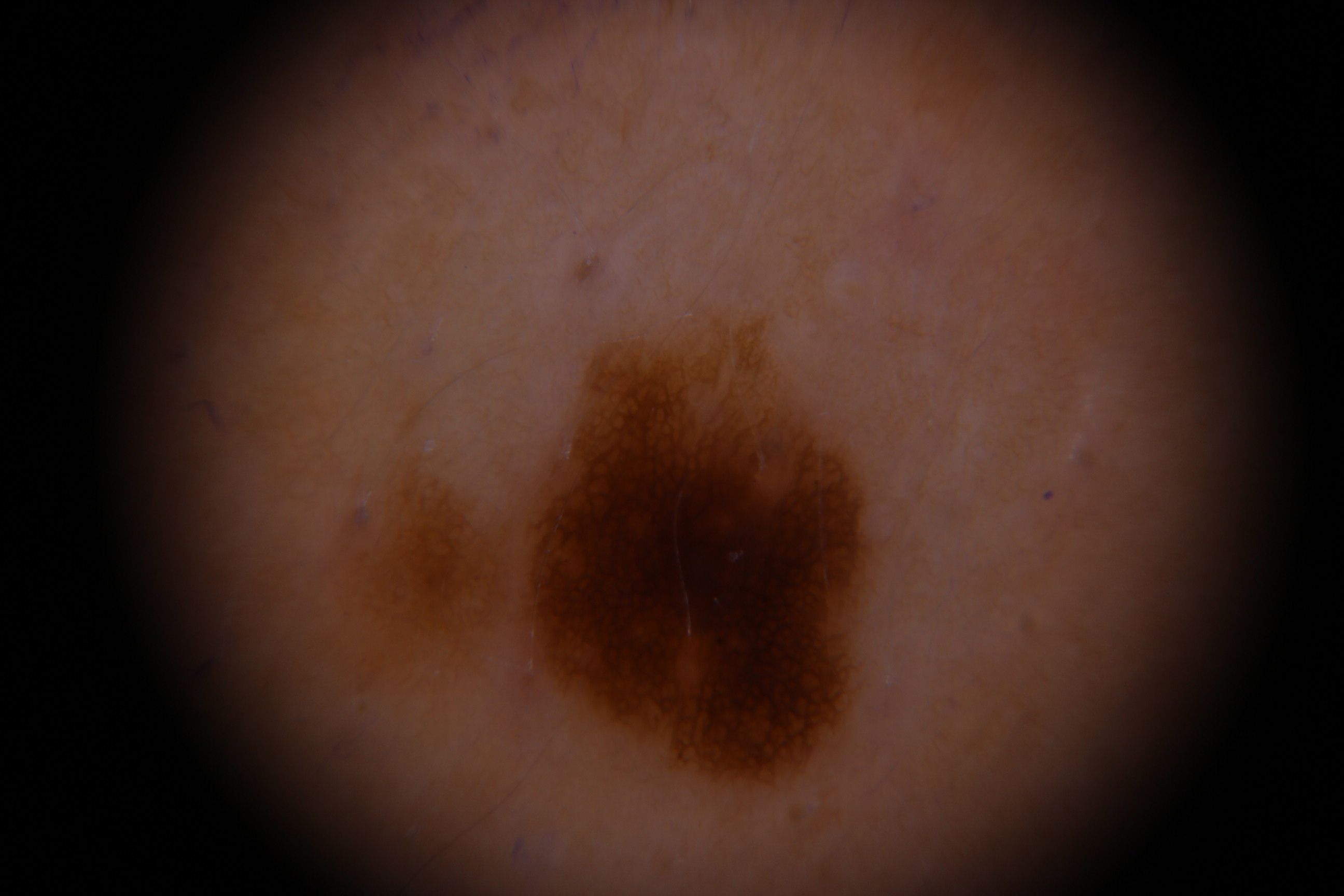Summary: A dermoscopic photograph of a skin lesion. Conclusion: The diagnostic label was a dysplastic junctional nevus.